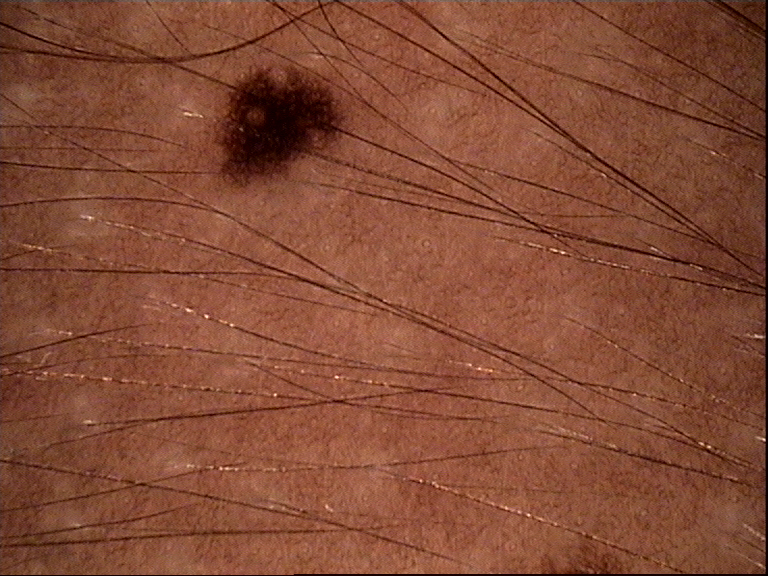Labeled as a dysplastic junctional nevus.